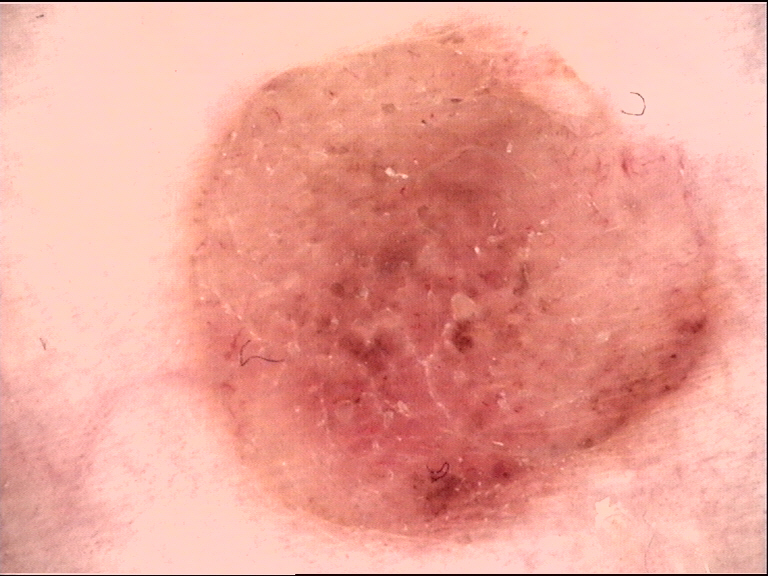A dermoscopic photograph of a skin lesion. The diagnosis was a banal lesion — a dermal nevus.